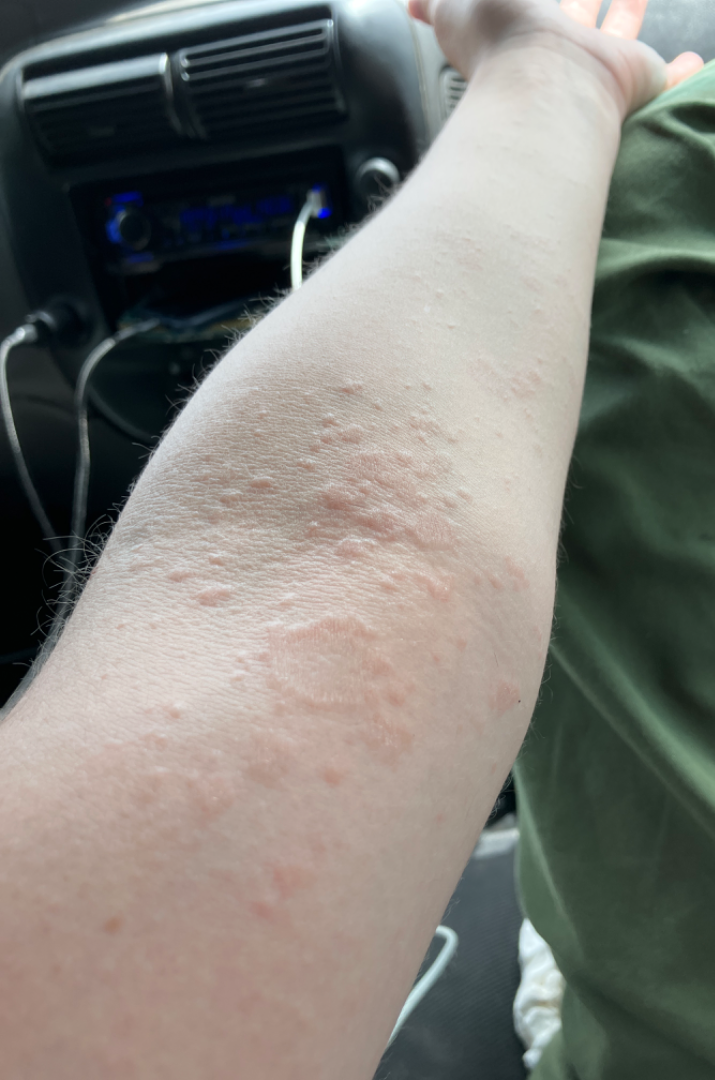Favoring Urticaria; less likely is Tinea Versicolor; less probable is Allergic Contact Dermatitis; a remote consideration is Eczema.